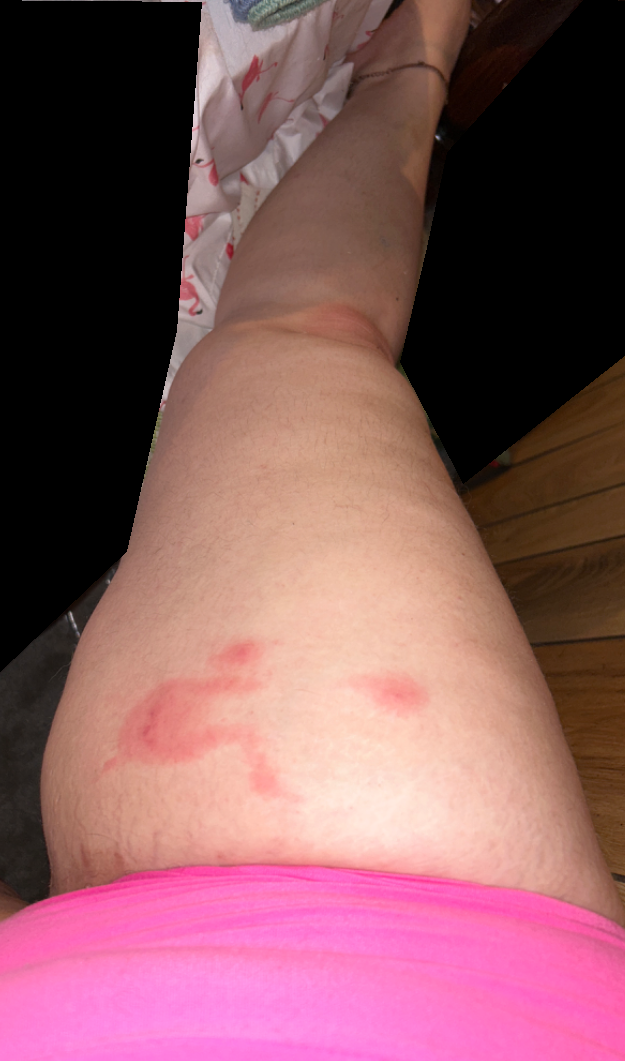<summary>
<assessment>not assessable</assessment>
<duration>less than one week</duration>
<skin_tone>
  <fitzpatrick>III</fitzpatrick>
</skin_tone>
<shot_type>at a distance</shot_type>
<body_site>leg</body_site>
<texture>raised or bumpy</texture>
<symptoms>burning, bothersome appearance, itching, enlargement, pain</symptoms>
</summary>